The chart records a prior melanoma; a male subject in their mid- to late 80s or older; the patient is skin type II; a dermoscopic photograph of a skin lesion: 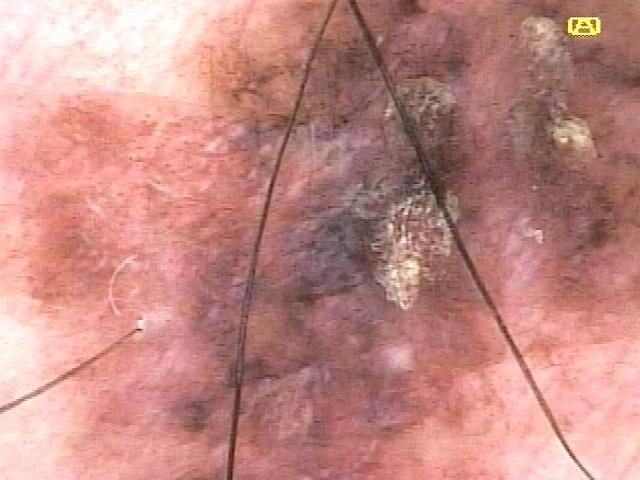{"lesion_location": {"region": "a lower extremity"}, "diagnosis": {"name": "Melanoma", "malignancy": "malignant", "confirmation": "histopathology"}}